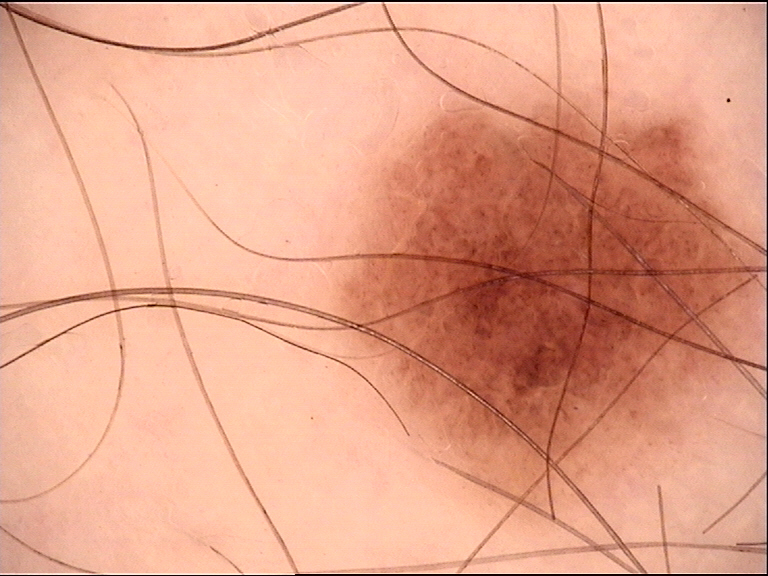- assessment · dysplastic junctional nevus (expert consensus)